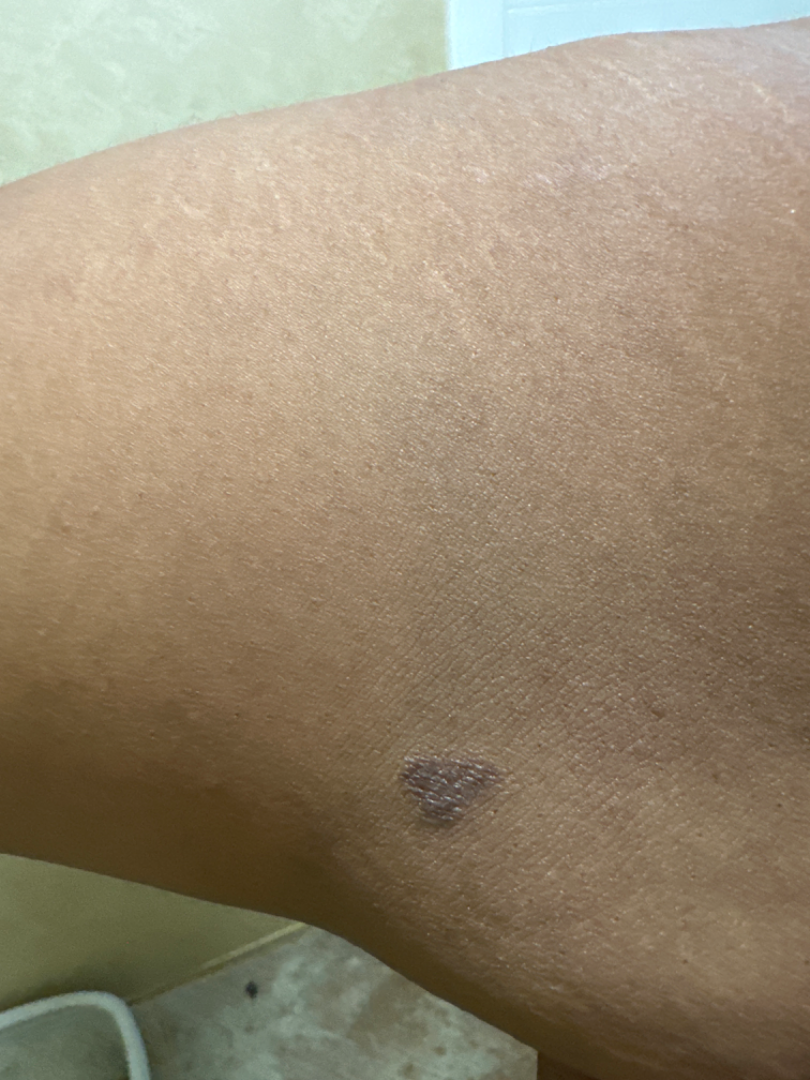| field | value |
|---|---|
| onset | one to three months |
| reported symptoms | bothersome appearance, itching, enlargement and darkening |
| location | arm |
| image framing | at an angle |
| surface texture | rough or flaky and flat |
| patient's own categorization | a rash |
| diagnostic considerations | SK/ISK (leading); Eczema (considered) |